A female subject age 59 · the patient says their skin reddens with sun exposure · the patient describes having a moderate number of moles · a dermoscopic image of a skin lesion · referred with a clinical suspicion of melanocytic nevus.
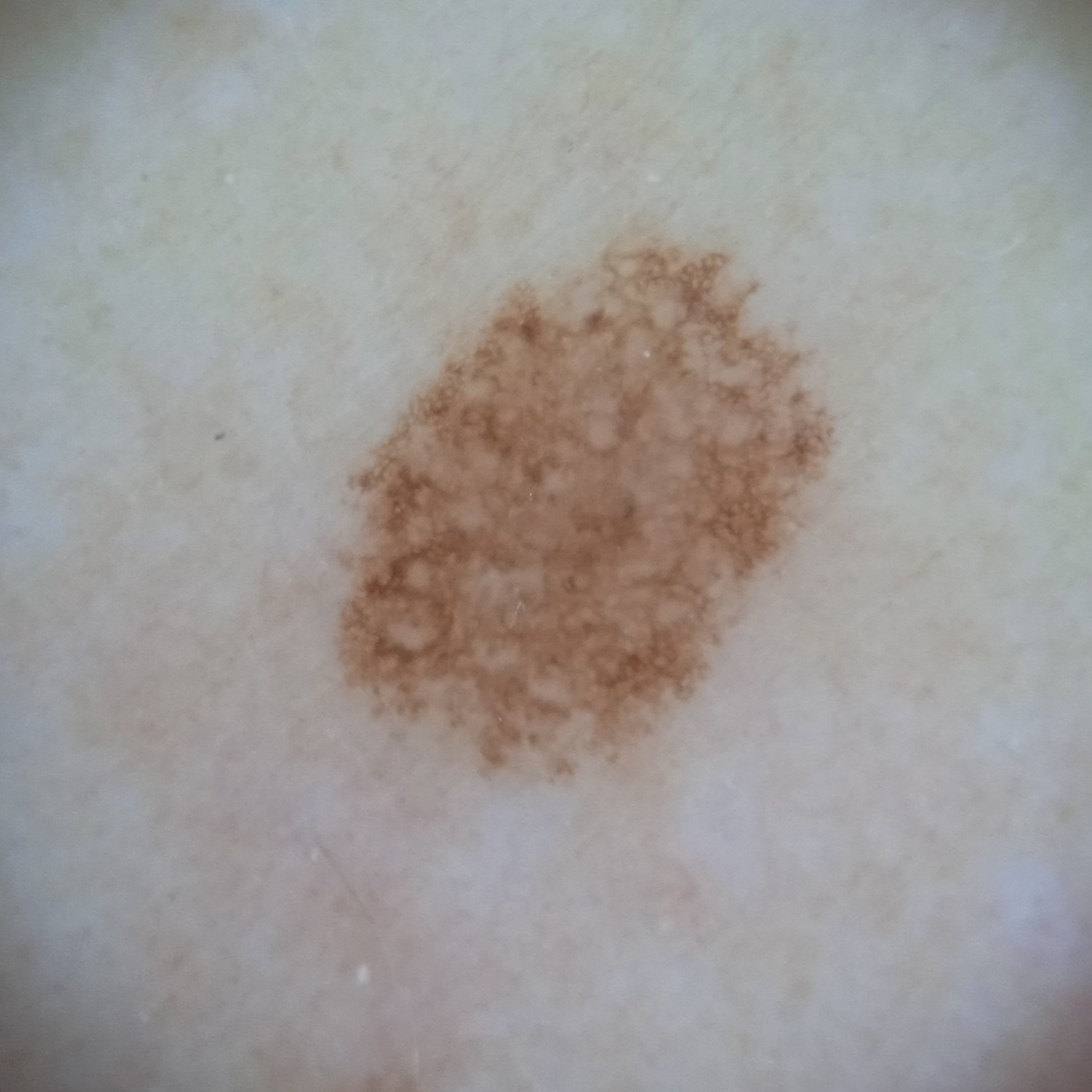Clinical context: Located on an arm. Pathology: On biopsy, the diagnosis was an atypical (dysplastic) nevus, following excision.